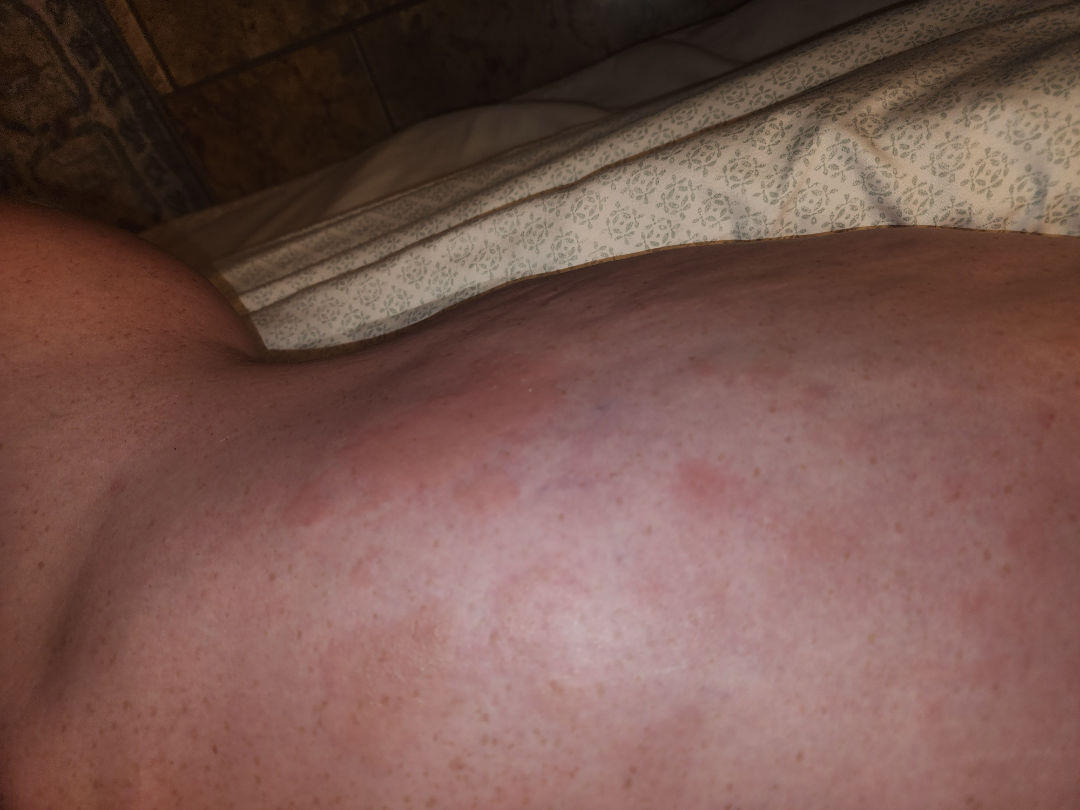* patient's own categorization · a rash
* lesion texture · raised or bumpy and fluid-filled
* framing · at an angle
* affected area · back of the hand, head or neck and leg
* patient · female, age 30–39
* reported symptoms · bothersome appearance, enlargement, itching and burning
* impression · most consistent with Urticaria; also consider Herpes Zoster; an alternative is Allergic Contact Dermatitis; a more distant consideration is Insect Bite